This is a close-up image.
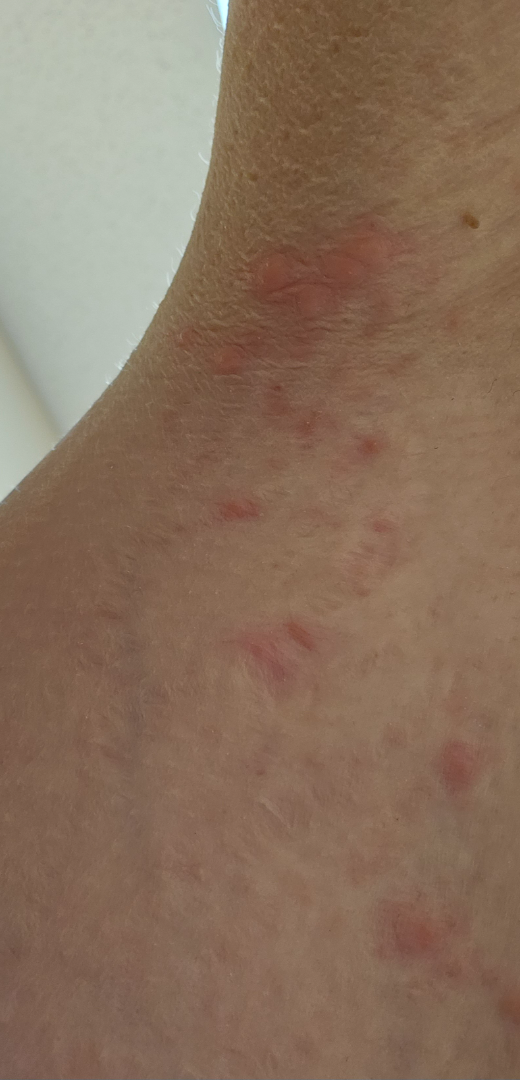History:
The lesion is described as raised or bumpy.
Impression:
On teledermatology review: Folliculitis (considered); Herpes Zoster (considered); Allergic Contact Dermatitis (considered).